Dermoscopy of a skin lesion: 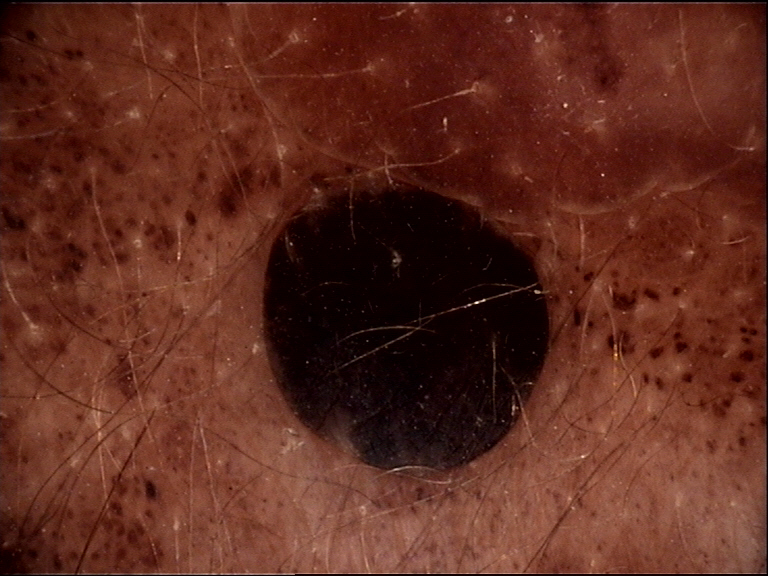Impression: Labeled as a banal lesion — a congenital compound nevus.